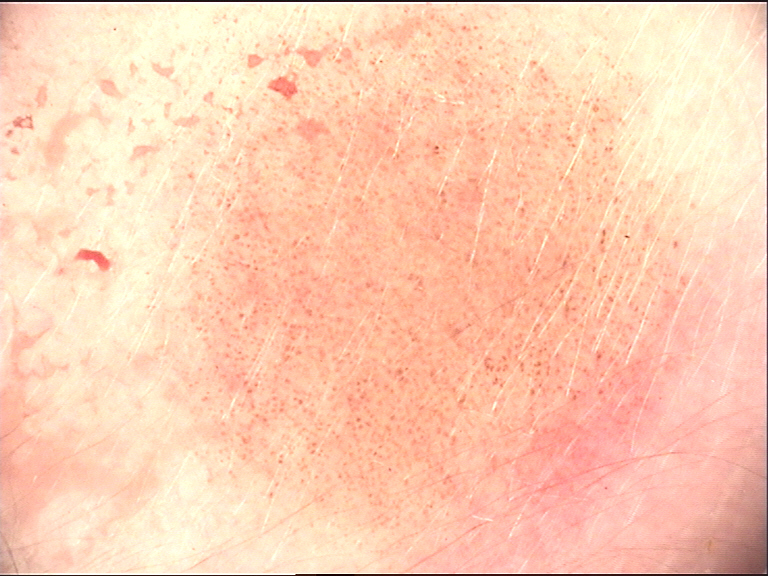The morphology is that of a banal lesion.
The diagnostic label was a congenital junctional nevus.